A dermoscopic photograph of a skin lesion:
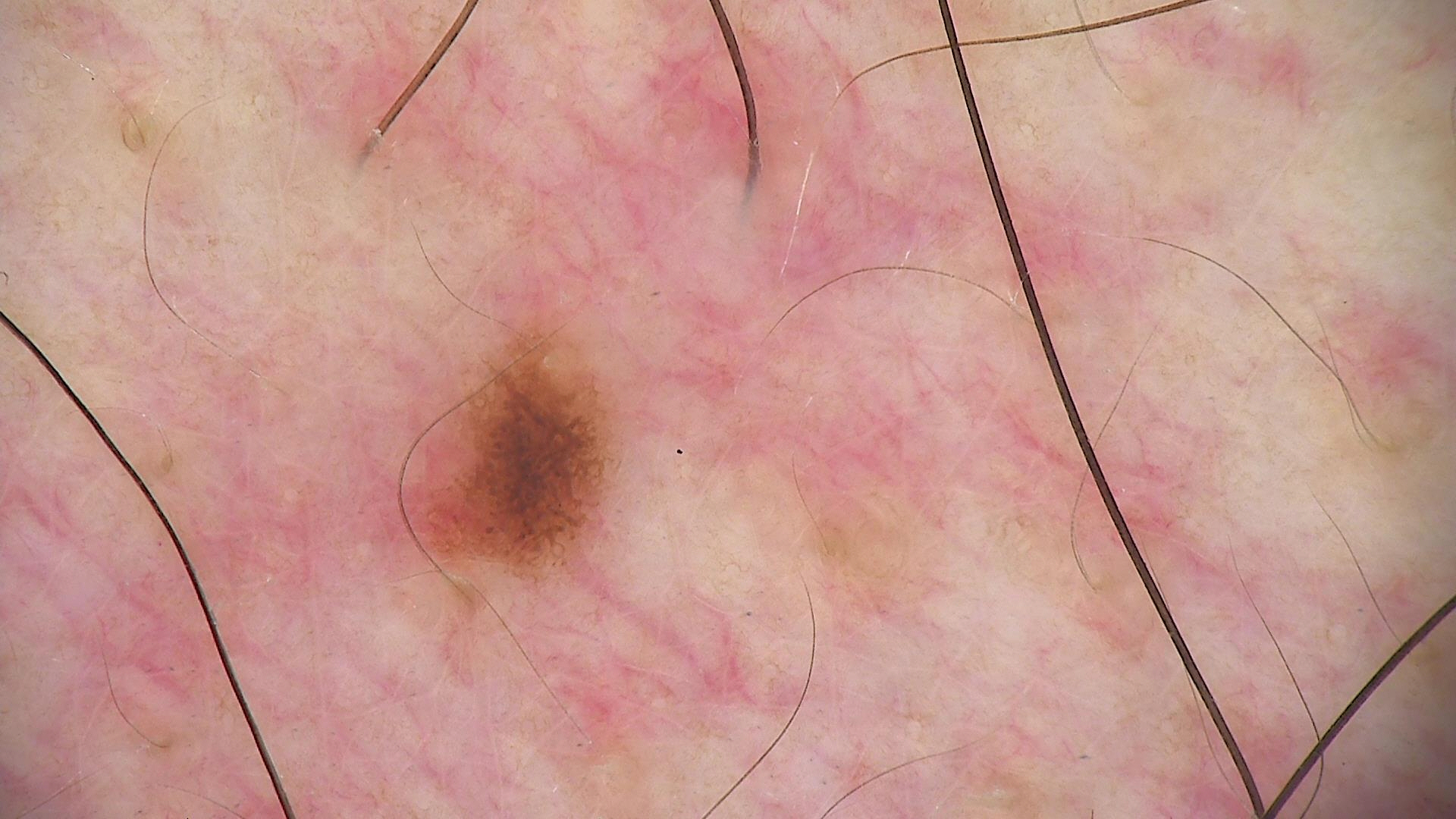Consistent with a dysplastic junctional nevus.